The patient considered this a rash, this is a close-up image, no constitutional symptoms were reported, texture is reported as fluid-filled and raised or bumpy, reported lesion symptoms include itching, the lesion involves the head or neck.
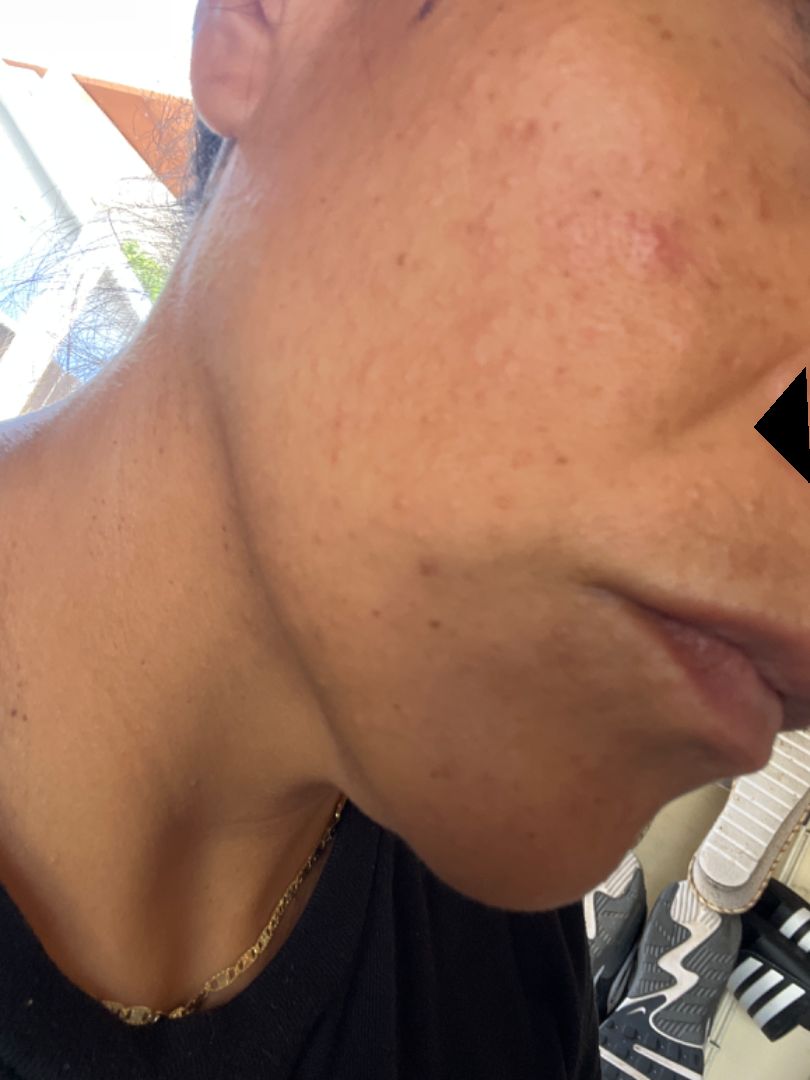Q: What conditions are considered?
A: favoring Acne